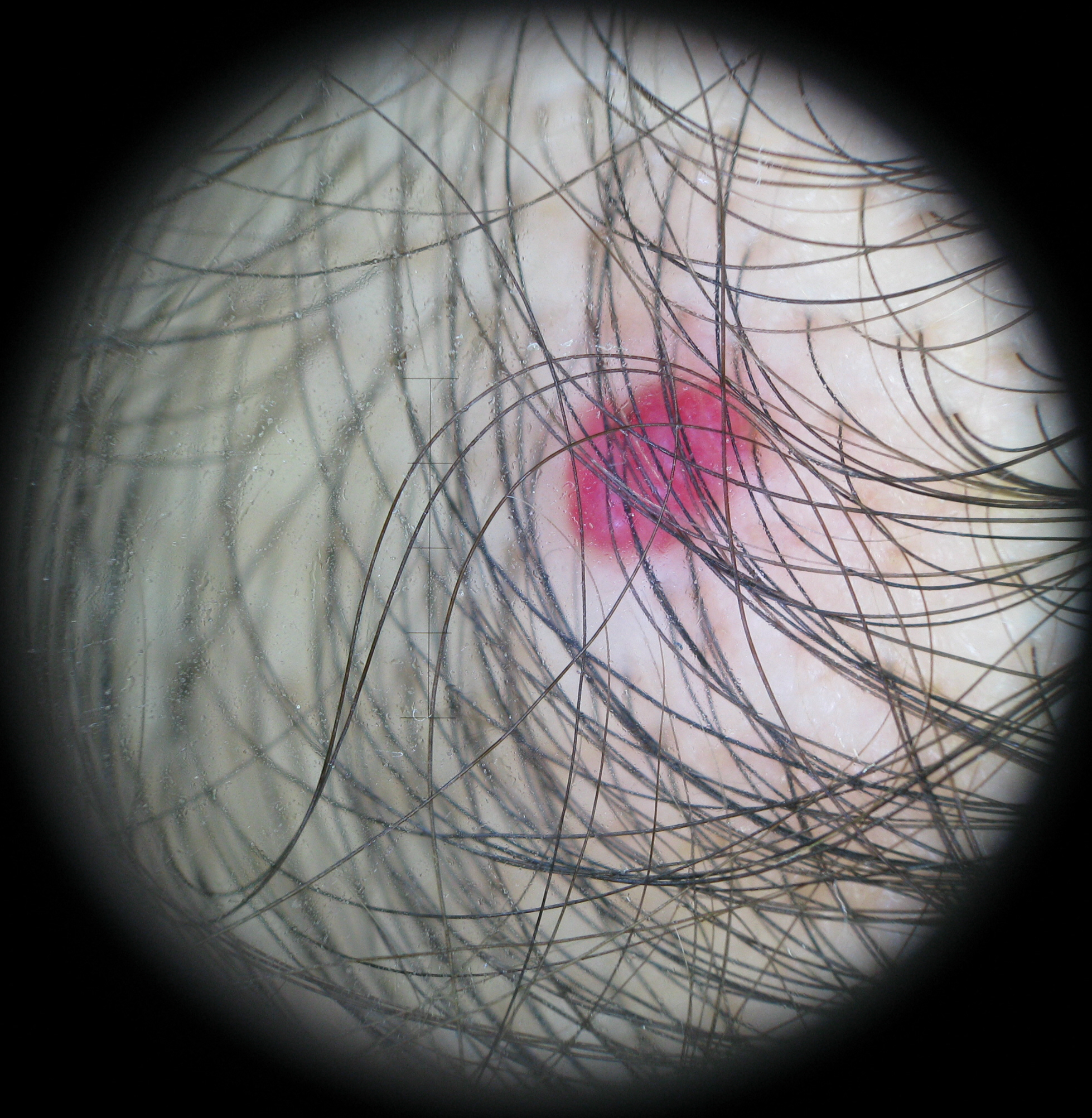imaging = dermatoscopy, lesion type = vascular, class = hemangioma (expert consensus).